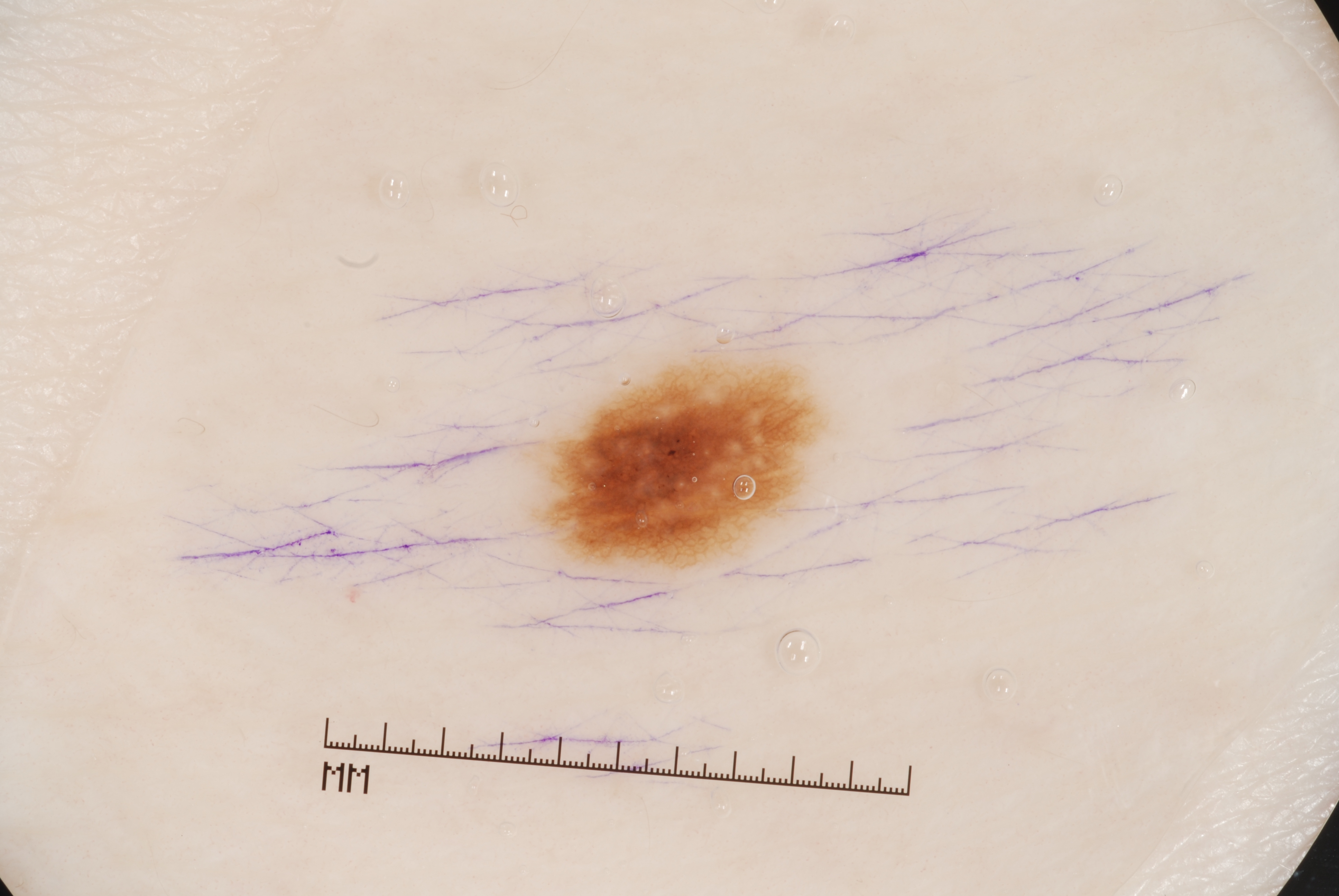Q: What kind of image is this?
A: dermatoscopic image of a skin lesion
Q: Who is the patient?
A: female, aged 58-62
Q: Which dermoscopic features were noted?
A: milia-like cysts and pigment network
Q: What is the lesion's bounding box?
A: (544, 357, 816, 567)
Q: How large is the lesion within the image?
A: ~4% of the field
Q: What is this lesion?
A: a melanocytic nevus, a benign lesion